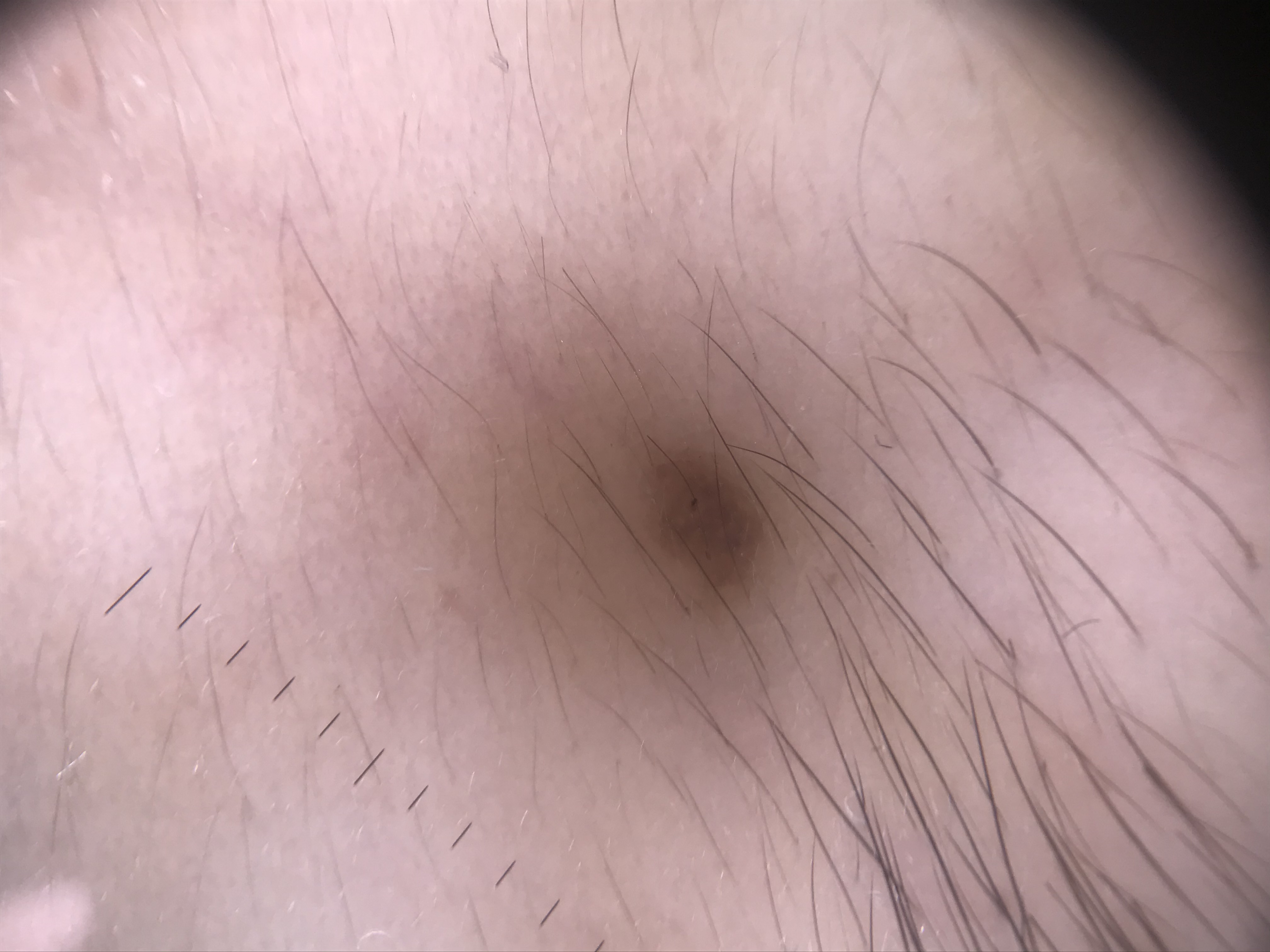A dermatoscopic image of a skin lesion. The morphology is that of a compound, banal lesion. Diagnosed as a Miescher nevus.